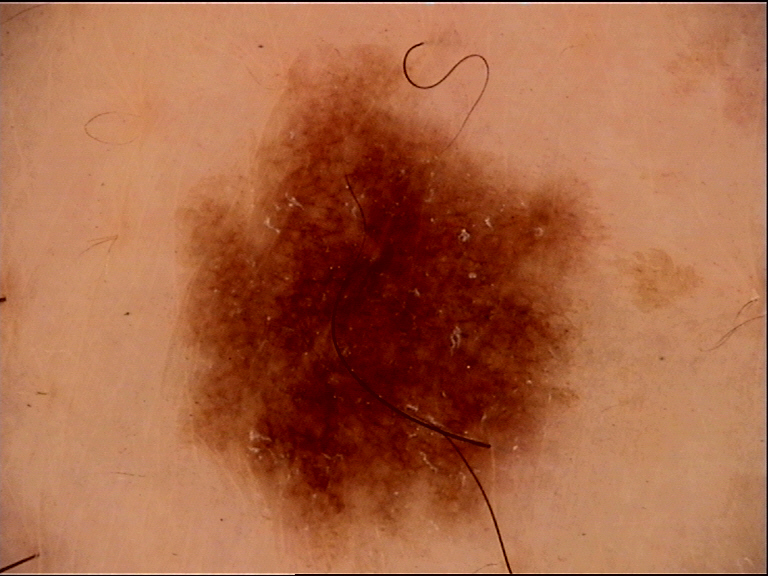Conclusion: Labeled as a dysplastic junctional nevus.